The patient is a female aged 50–59 · the front of the torso and back of the torso are involved · no constitutional symptoms were reported · a close-up photograph · the patient described the issue as skin that appeared healthy to them · the contributor notes the lesion is raised or bumpy and rough or flaky · reported lesion symptoms include enlargement, itching and bothersome appearance · the condition has been present for less than one week: 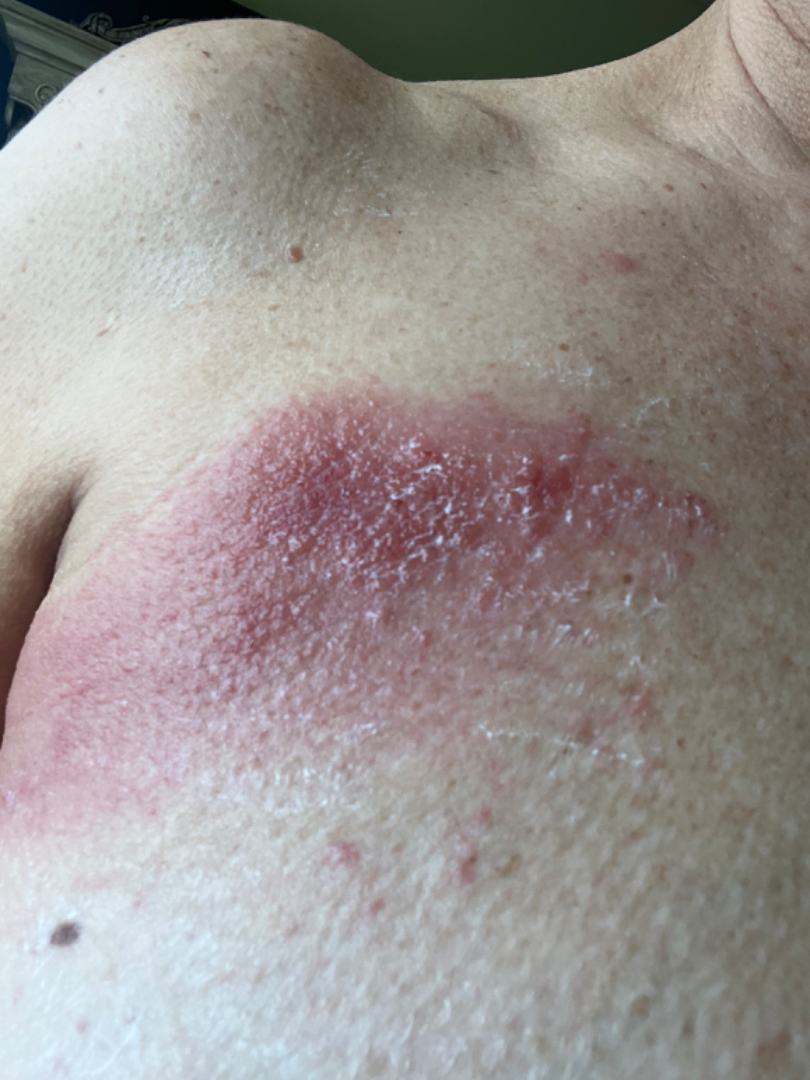The case was difficult to assess from the available photograph.